The lesion is described as rough or flaky; the contributor is a female aged 40–49; the patient indicates associated fatigue and joint pain; the lesion involves the arm, back of the torso and leg; the lesion is associated with bothersome appearance, itching, bleeding and enlargement; the photo was captured at an angle; the patient considered this a rash; the patient indicates the condition has been present for one to three months:
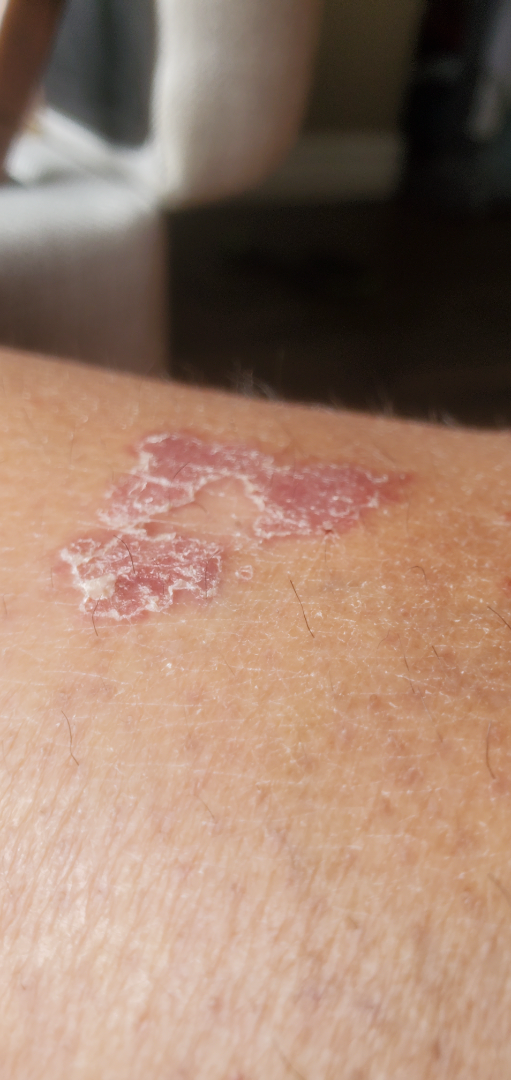Review:
On photographic review, most likely Psoriasis; also on the differential is Lichen planus/lichenoid eruption; a more distant consideration is Porokeratosis.